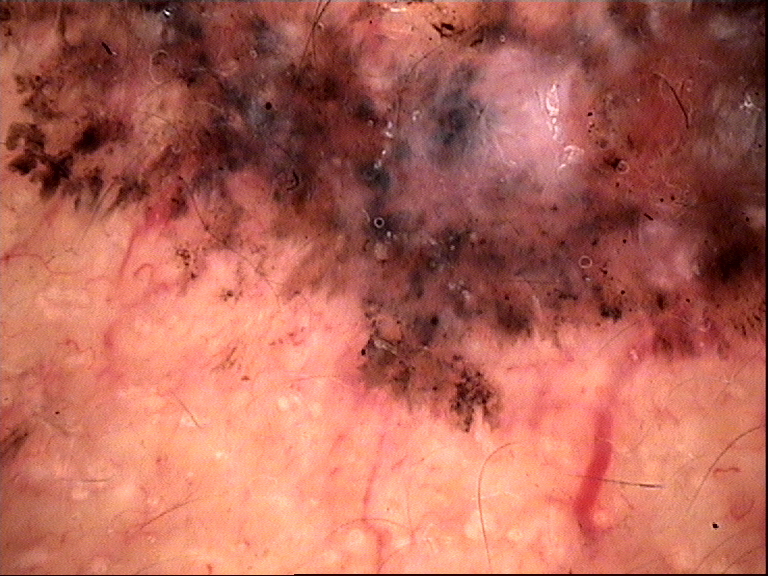image type: dermoscopy
class: basal cell carcinoma (biopsy-proven)